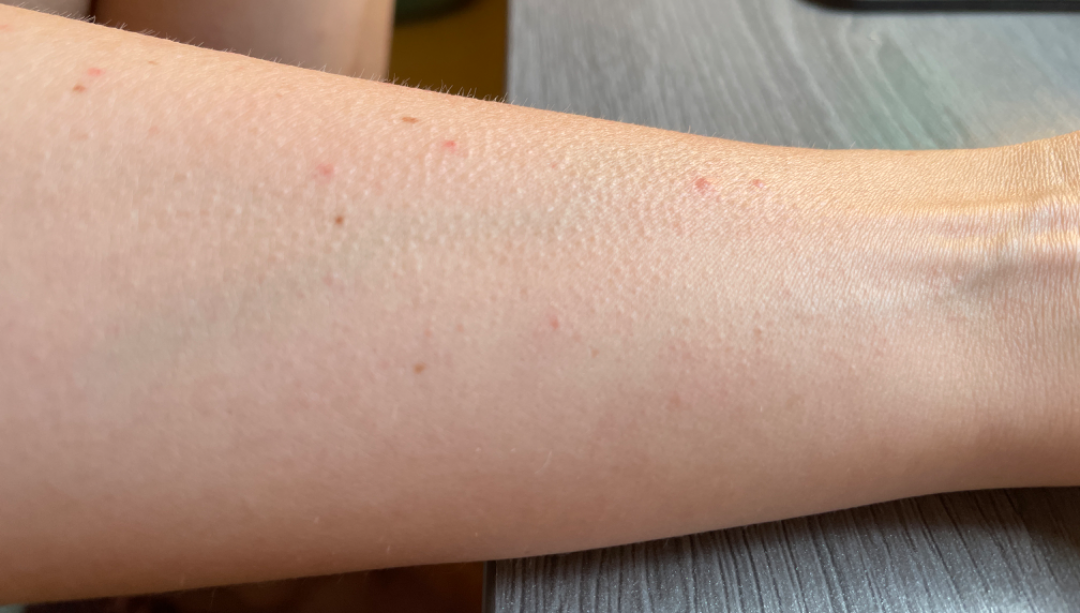Review: No differential diagnosis could be assigned on photographic review.